The subject is 50–59, female. The top or side of the foot and leg are involved. The photograph was taken at an angle.
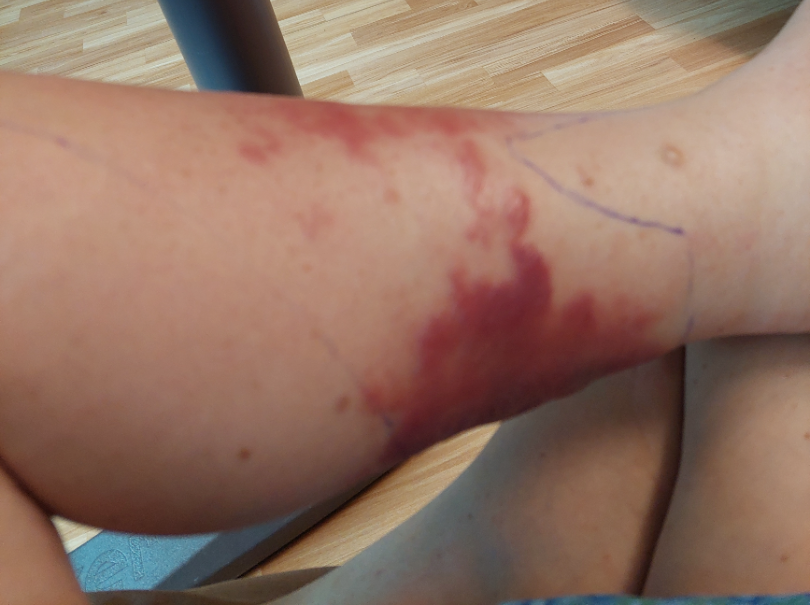| feature | finding |
|---|---|
| clinical impression | Skin and soft tissue atypical mycobacterial infection (considered); hemorrhagic bullae (considered); Bullous dermatitis, NOS (lower probability) |